The contributor is 18–29, male · this image was taken at a distance · the arm, head or neck and front of the torso are involved: 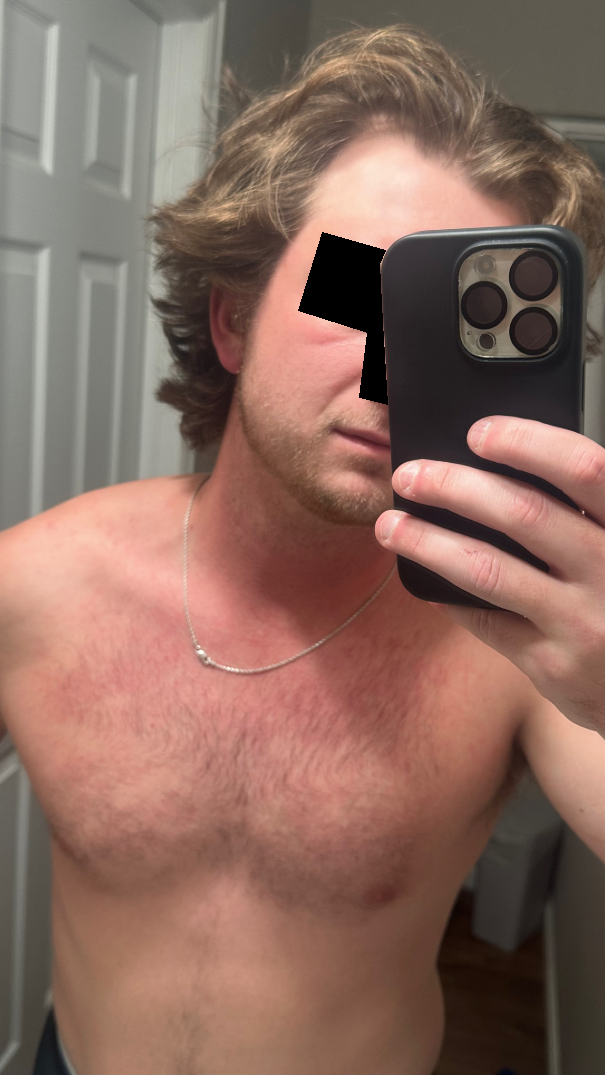Q: Could the case be diagnosed?
A: indeterminate
Q: Texture?
A: flat
Q: How does the patient describe it?
A: a rash
Q: Constitutional symptoms?
A: chills, joint pain, mouth sores, shortness of breath, fatigue and fever
Q: Reported symptoms?
A: bothersome appearance